Dermoscopy of a skin lesion.
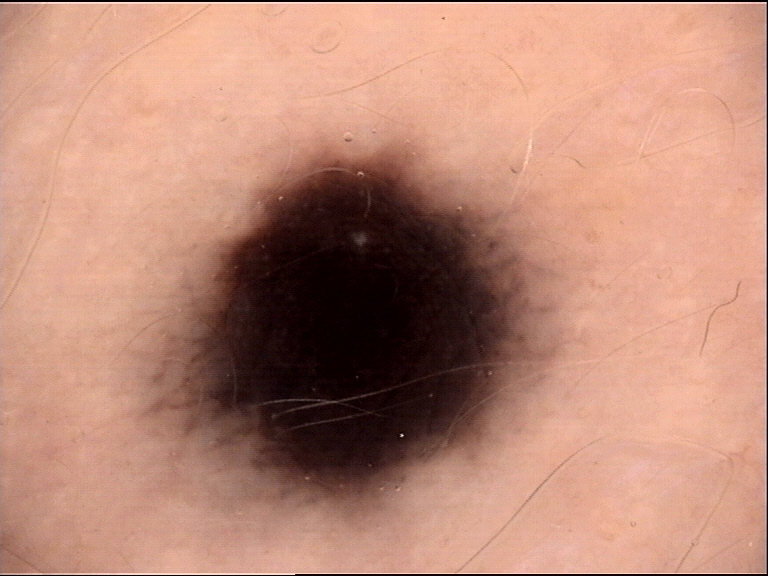– diagnostic label — blue nevus (expert consensus)